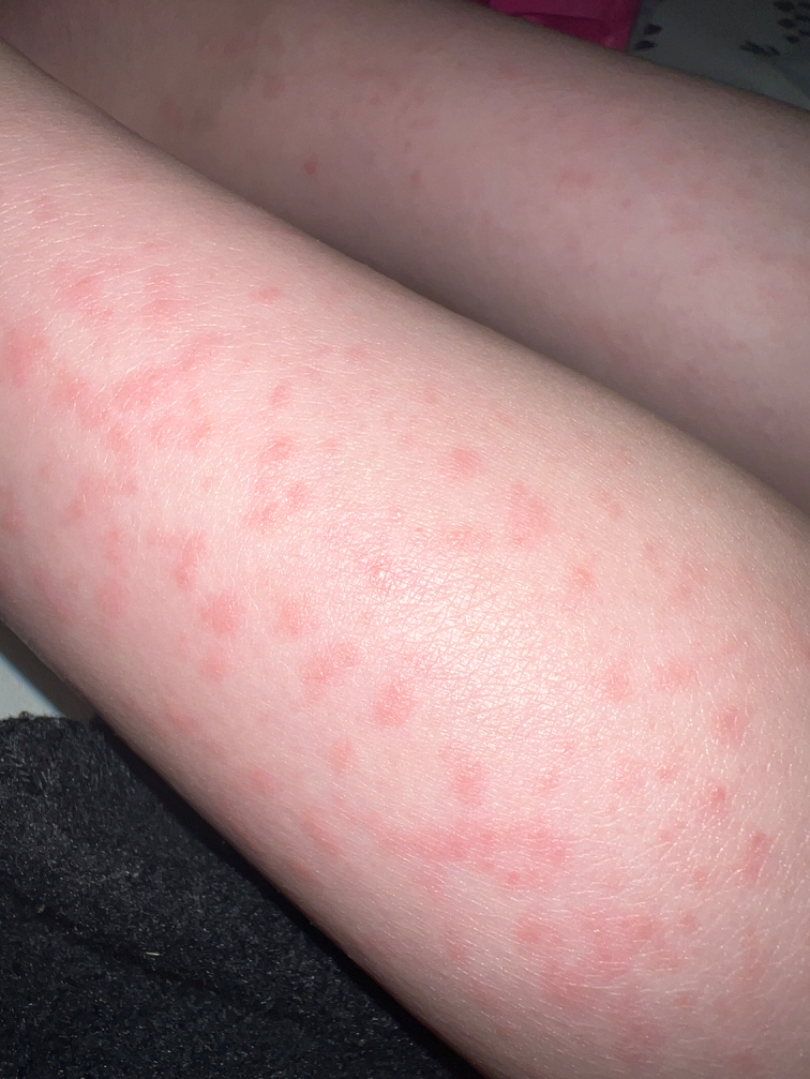Background: The photograph is a close-up of the affected area. Present for about one day. Located on the front of the torso, back of the torso, leg and arm. Reported lesion symptoms include bothersome appearance and itching. The contributor notes the lesion is raised or bumpy. Findings: The favored diagnosis is Viral Exanthem; the differential also includes Drug Rash.